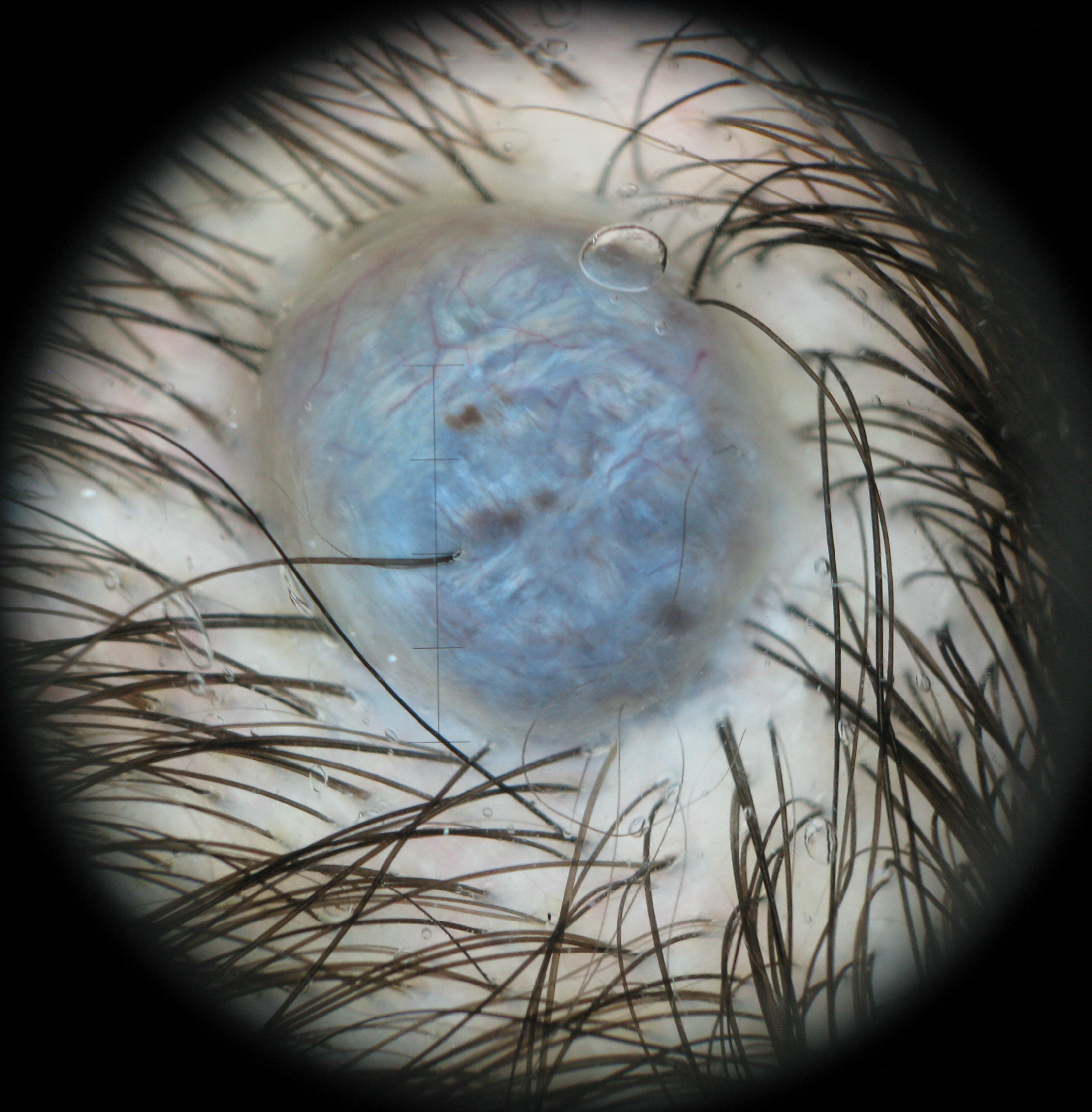• label — blue nevus (expert consensus)